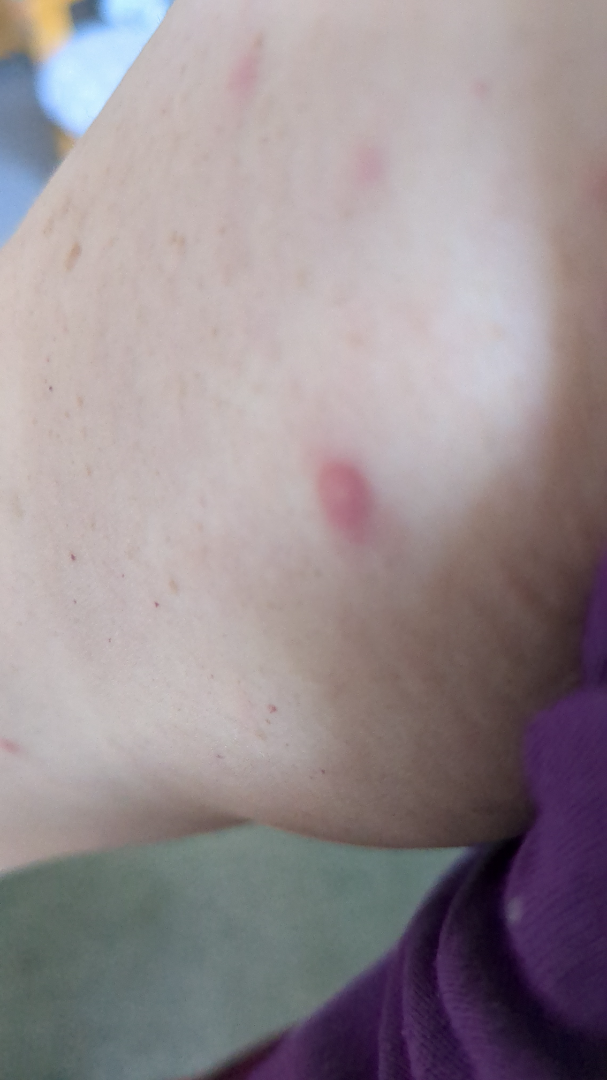{"assessment": "unable to determine", "shot_type": "close-up", "body_site": "arm", "systemic_symptoms": "none reported", "patient_category": "a rash", "symptoms": "bothersome appearance", "duration": "less than one week", "texture": "raised or bumpy"}